A patient aged 73. A clinical close-up photograph of a skin lesion.
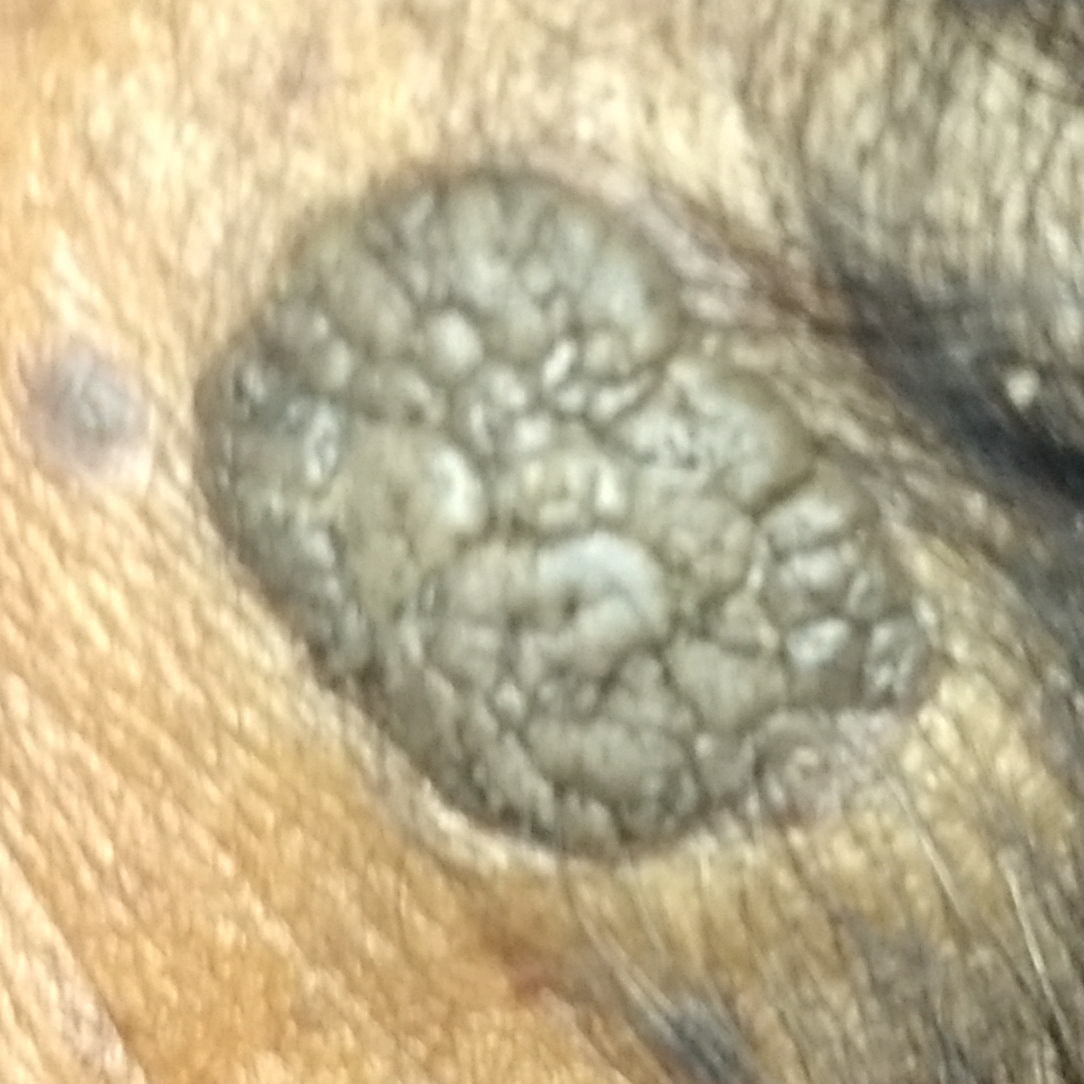Q: Where on the body is the lesion?
A: the face
Q: What symptoms does the patient report?
A: elevation
Q: What is this lesion?
A: seborrheic keratosis (clinical consensus)